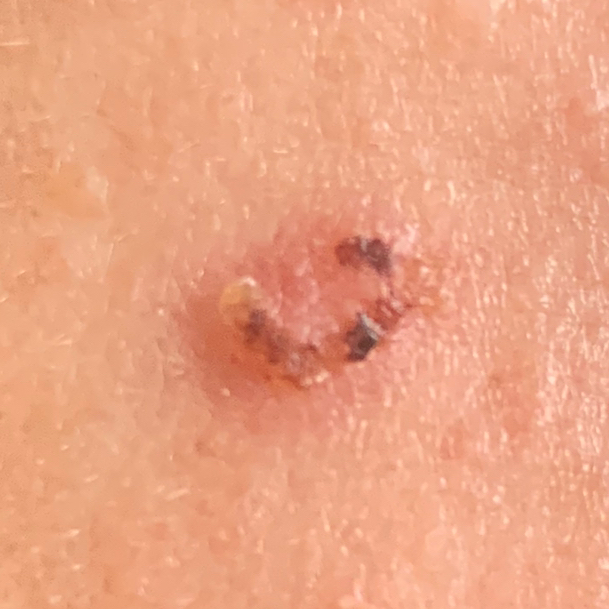Q: What kind of image is this?
A: clinical photo
Q: Who is the patient?
A: male, 55 years of age
Q: What is the anatomic site?
A: the face
Q: What symptoms does the patient report?
A: elevation, bleeding, itching
Q: What is this lesion?
A: basal cell carcinoma (biopsy-proven)